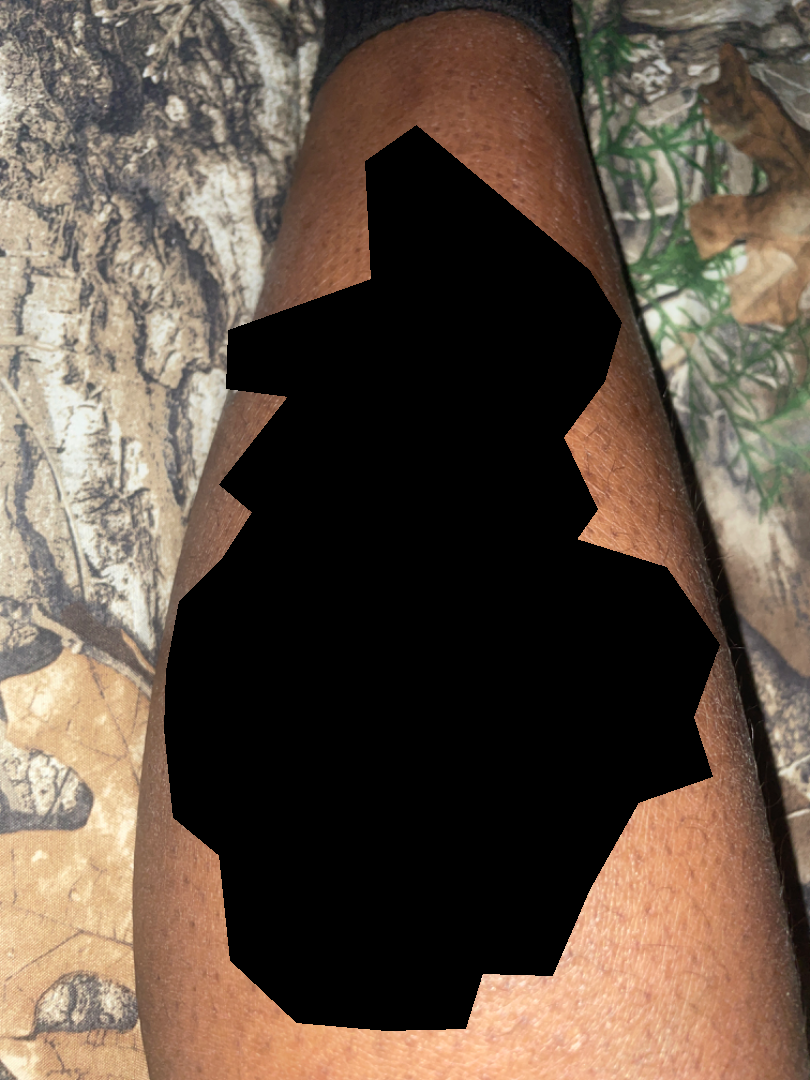| field | value |
|---|---|
| assessment | not assessable |
| symptom duration | one to three months |
| photo taken | at an angle |
| anatomic site | leg |